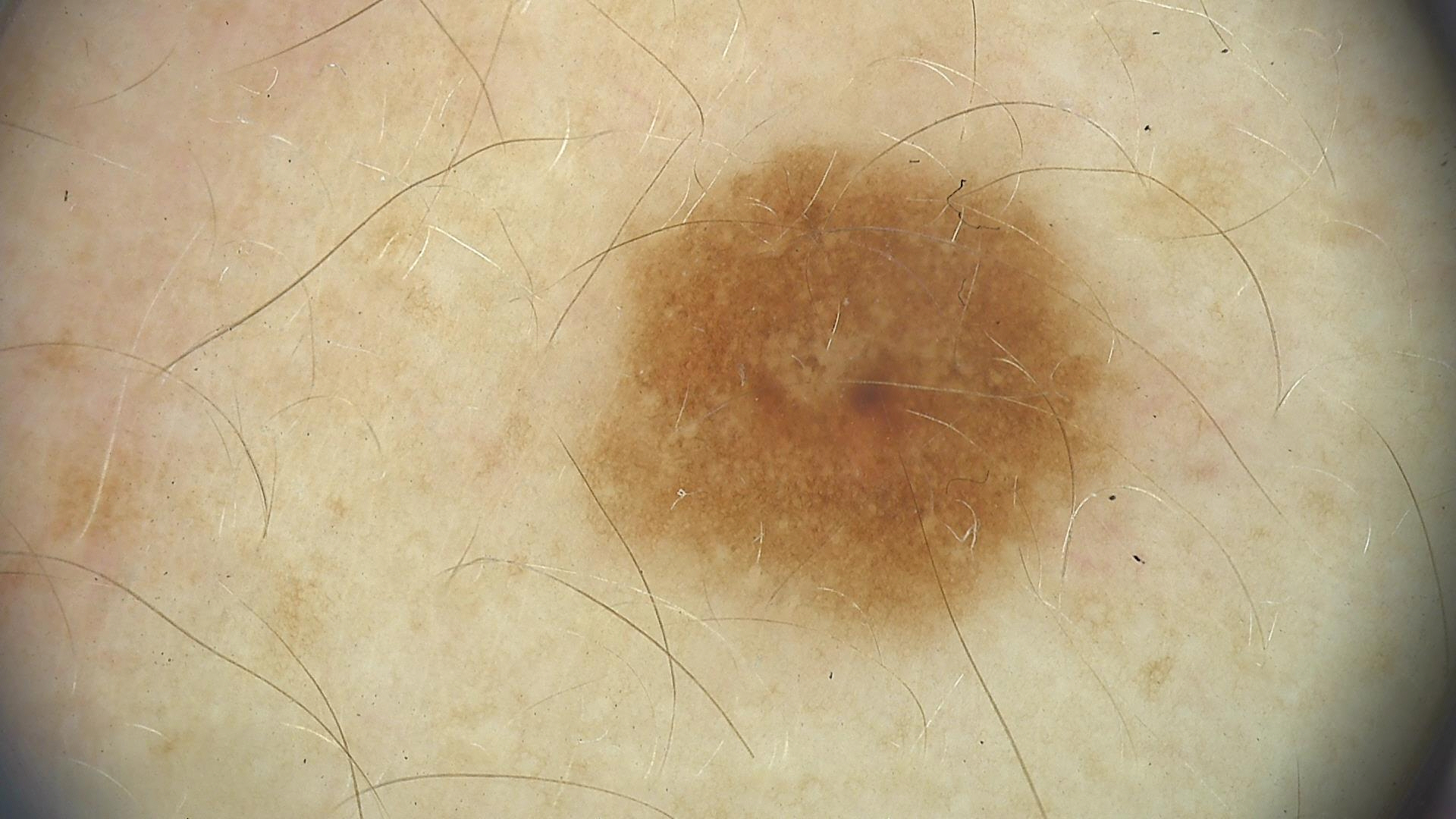A skin lesion imaged with a dermatoscope.
Consistent with a dysplastic compound nevus.